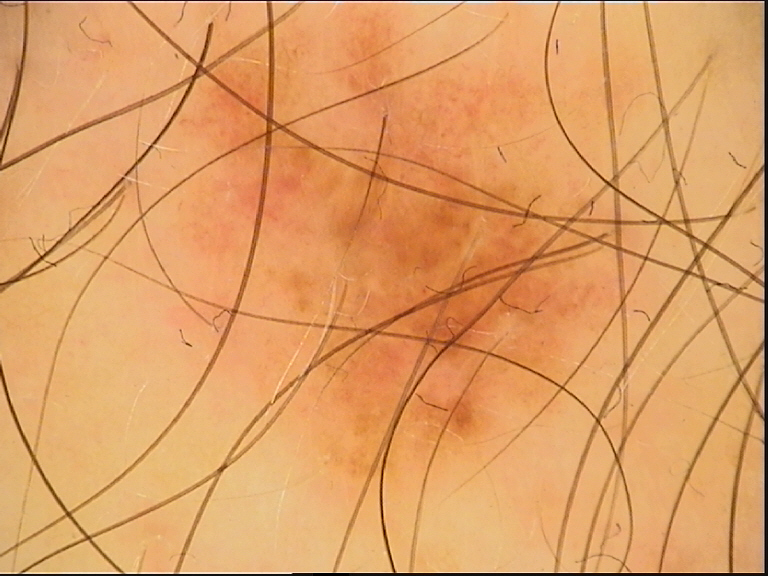Case:
A dermoscopy image of a single skin lesion.
Impression:
Classified as a benign lesion — a dysplastic compound nevus.